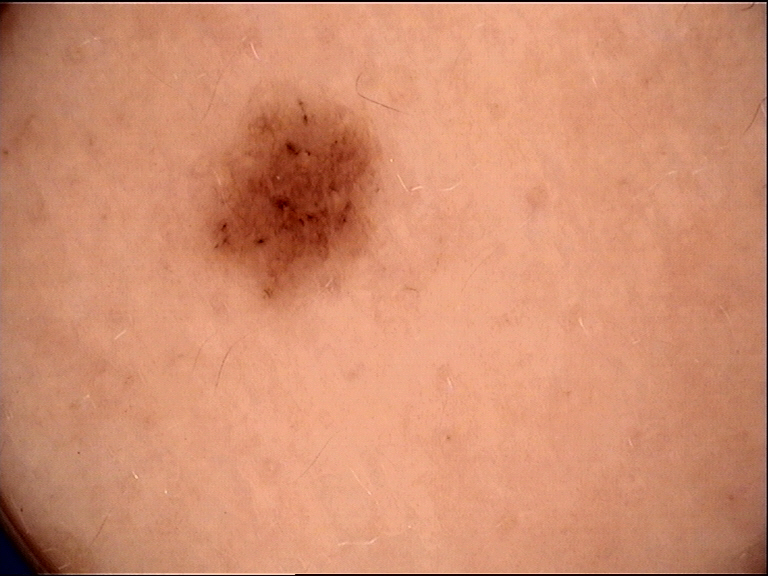image = dermatoscopy; label = dysplastic junctional nevus (expert consensus).